A dermoscopic image of a skin lesion.
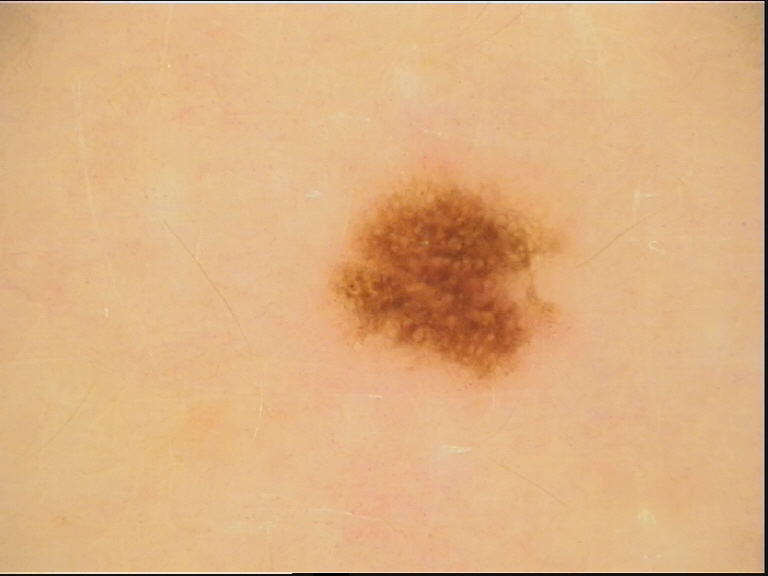<lesion>
  <diagnosis>
    <name>dysplastic junctional nevus</name>
    <code>jd</code>
    <malignancy>benign</malignancy>
    <super_class>melanocytic</super_class>
    <confirmation>expert consensus</confirmation>
  </diagnosis>
</lesion>